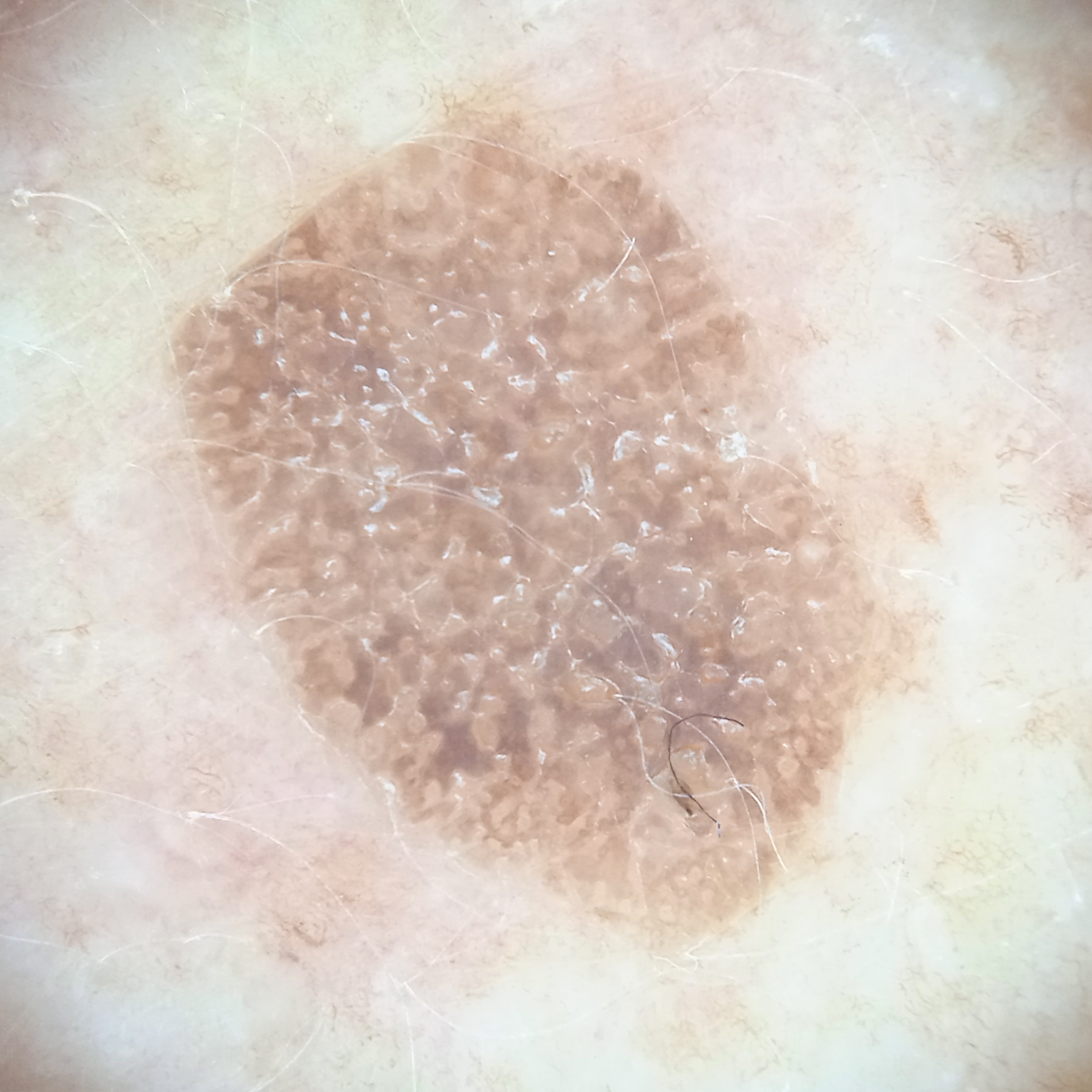{
  "patient": {
    "age": 78,
    "sex": "female"
  },
  "referral": "research study (no referral diagnosis)",
  "mole_burden": "numerous melanocytic nevi",
  "image": "dermoscopy",
  "lesion_location": "the back",
  "lesion_size": {
    "diameter_mm": 9.6
  },
  "diagnosis": {
    "name": "seborrheic keratosis",
    "malignancy": "benign"
  }
}